An image taken at a distance: 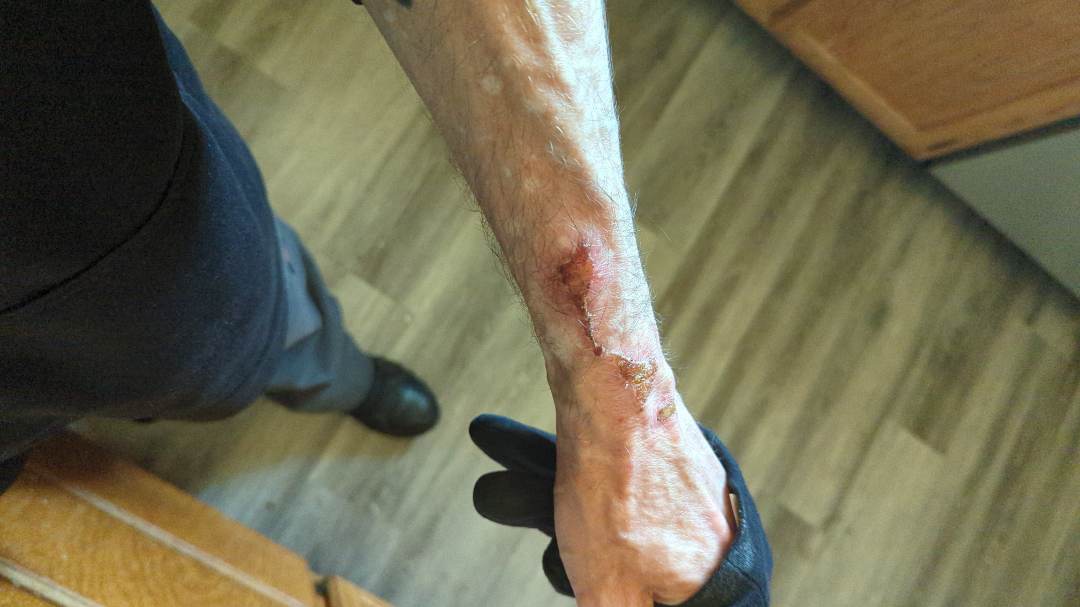Notes:
* skin tone · Fitzpatrick phototype II; human graders estimated Monk Skin Tone 2 or 3
* differential diagnosis · single-reviewer assessment: most consistent with Impetigo; with consideration of Bullous Pemphigoid